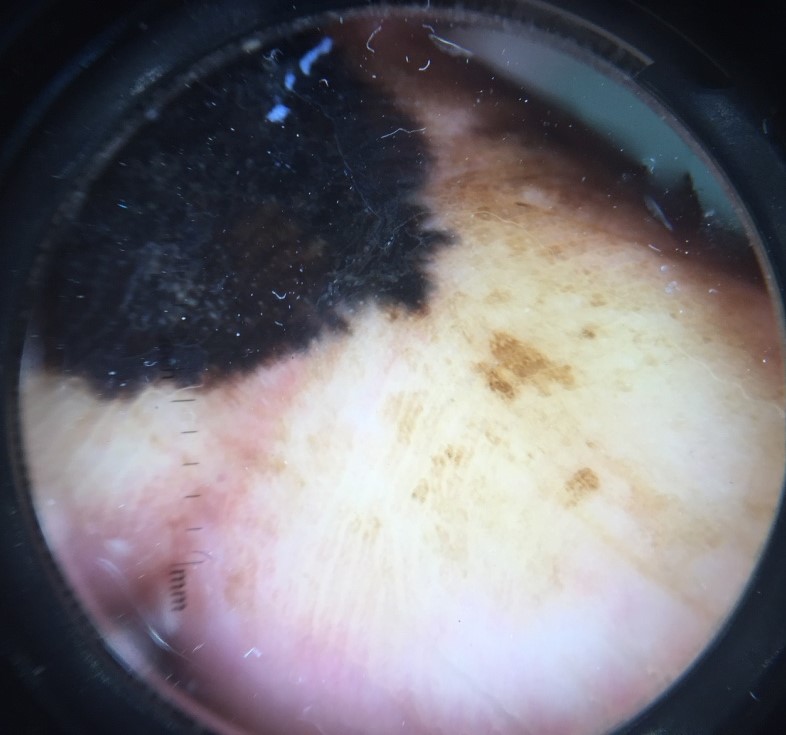Dermoscopy of a skin lesion. Histopathologically confirmed as a skin cancer — an acral lentiginous melanoma.